The patient is a female aged 18–29 · the contributor reports the lesion is raised or bumpy and rough or flaky · self-categorized by the patient as a rash · the photograph is a close-up of the affected area · the condition has been present for one to three months · located on the arm and leg — 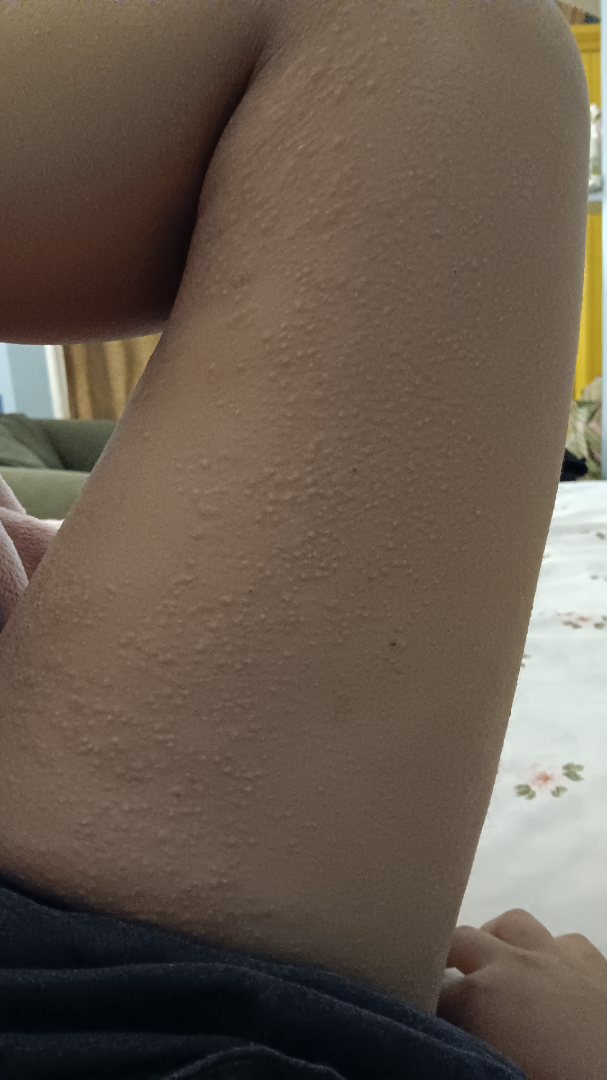Impression: On dermatologist assessment of the image, the primary impression is Eczema; an alternative is Urticaria; possibly Allergic Contact Dermatitis.